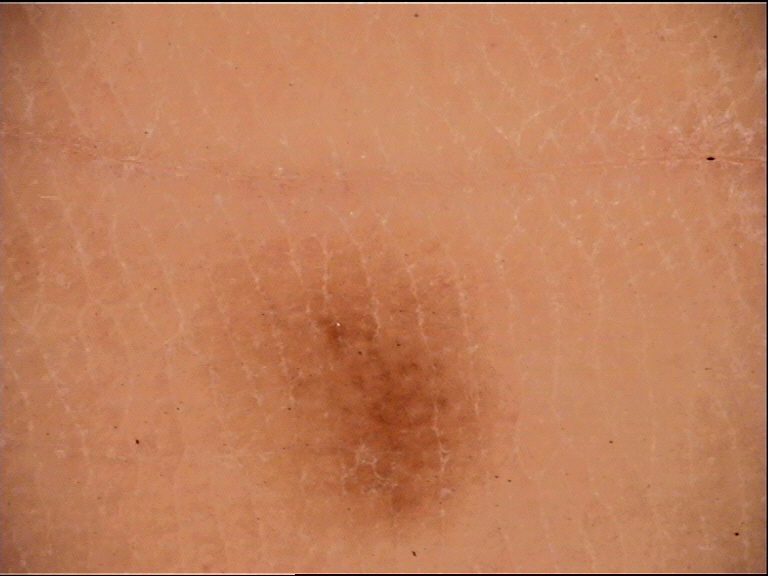* classification — banal
* diagnostic label — acral junctional nevus (expert consensus)